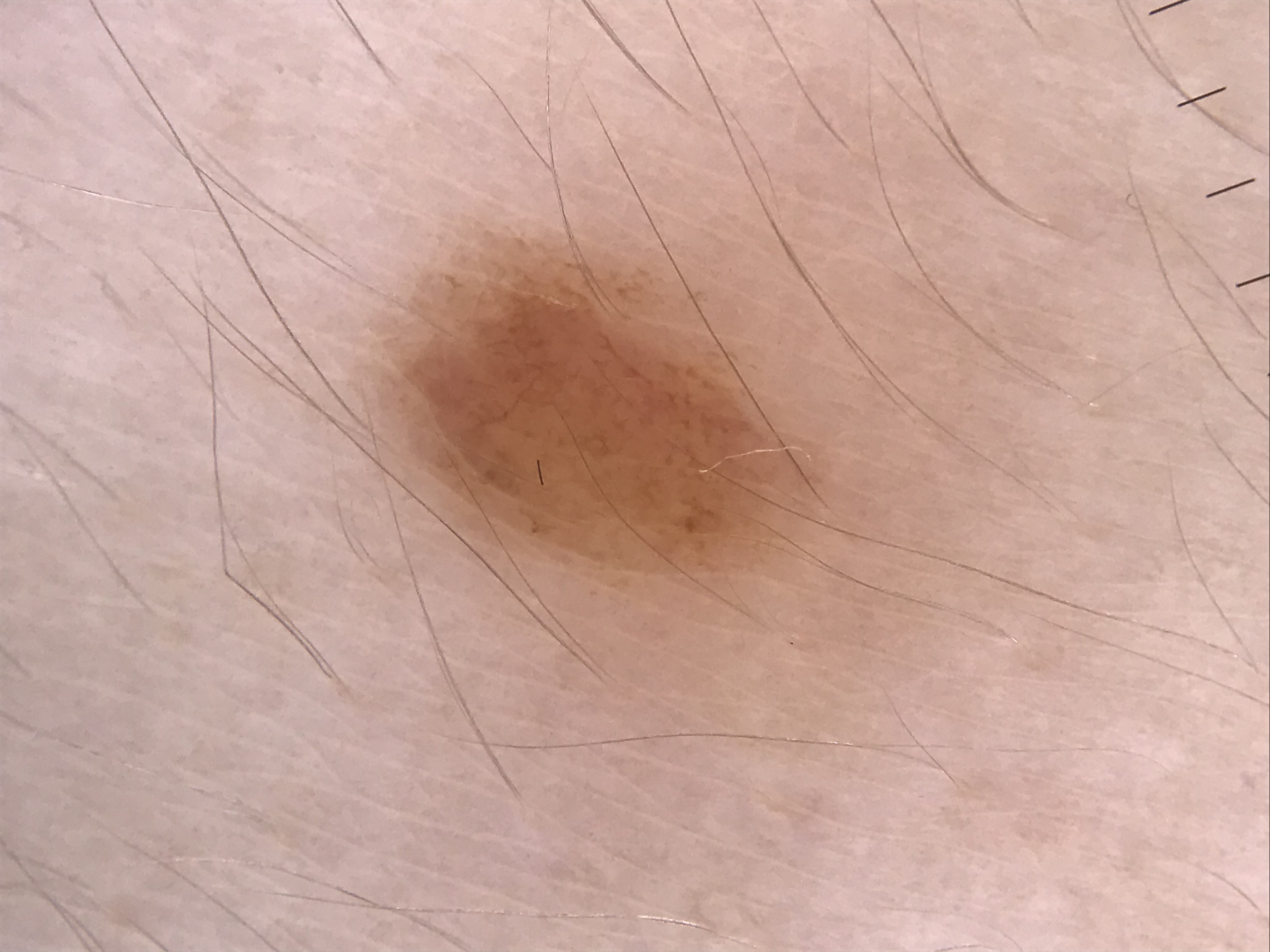Diagnosed as a banal lesion — a junctional nevus.